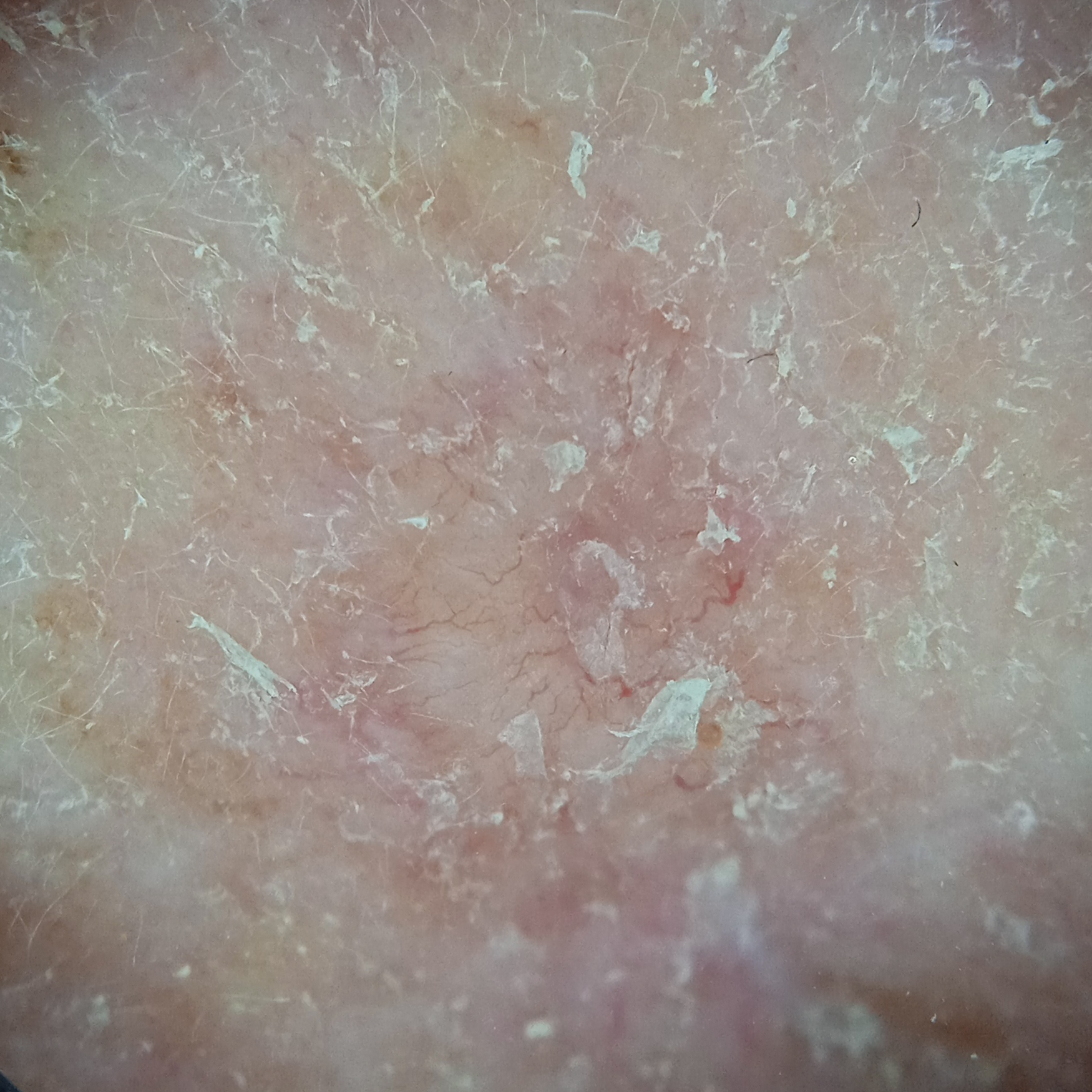Collected as part of a research study, without a referral diagnosis. Dermoscopy of a skin lesion. By self-report, a personal history of cancer and a family history of skin cancer. The lesion involves the face. The lesion is about 7 mm across. The consensus diagnosis for this lesion was a basal cell carcinoma.